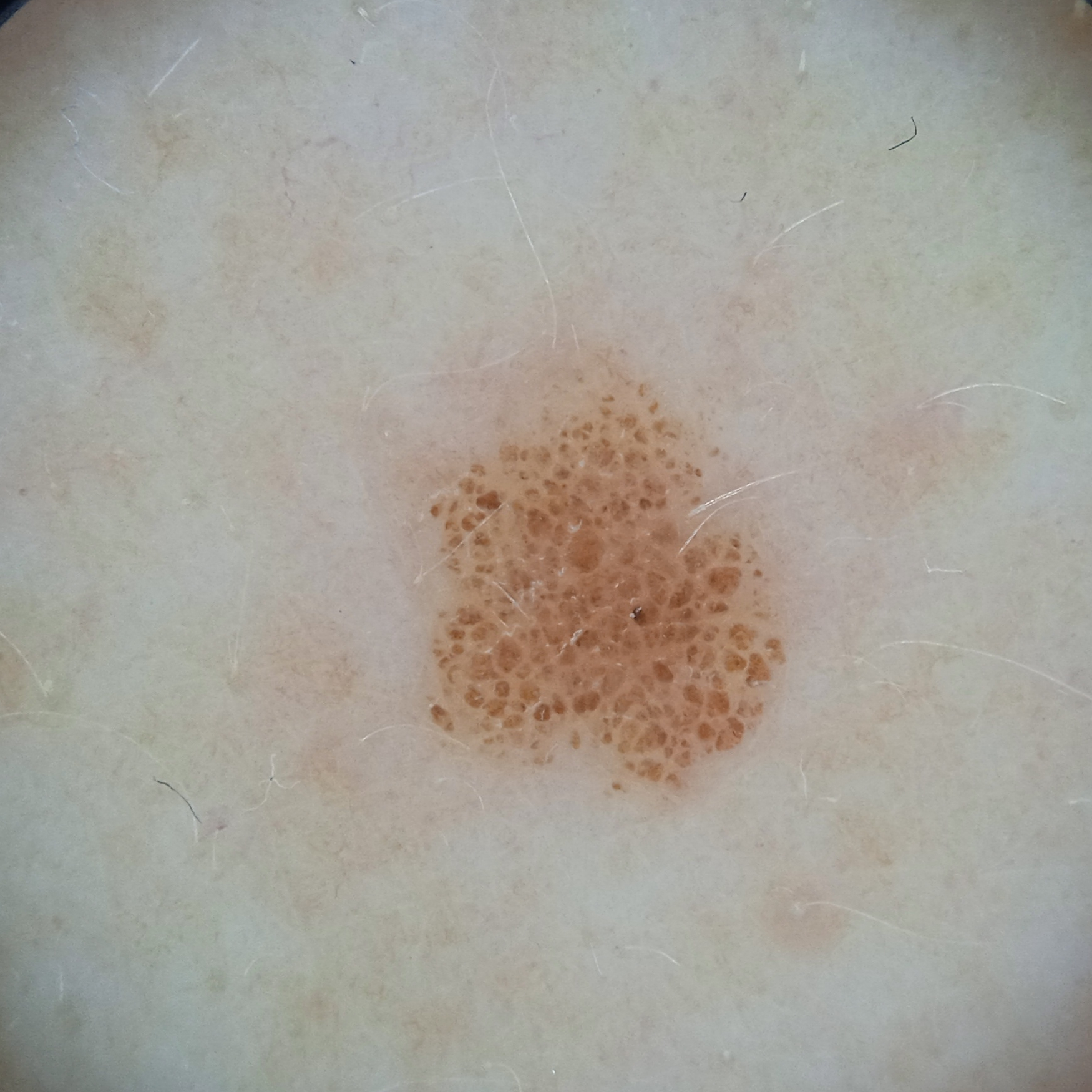<skin_lesion>
  <mole_burden>a moderate number of melanocytic nevi</mole_burden>
  <image>dermoscopy</image>
  <sun_reaction>skin reddens with sun exposure</sun_reaction>
  <referral>research study (no referral diagnosis)</referral>
  <lesion_location>the back</lesion_location>
  <lesion_size>
    <diameter_mm>5.1</diameter_mm>
  </lesion_size>
  <diagnosis>
    <name>melanocytic nevus</name>
    <malignancy>benign</malignancy>
  </diagnosis>
</skin_lesion>